A dermoscopy image of a single skin lesion:
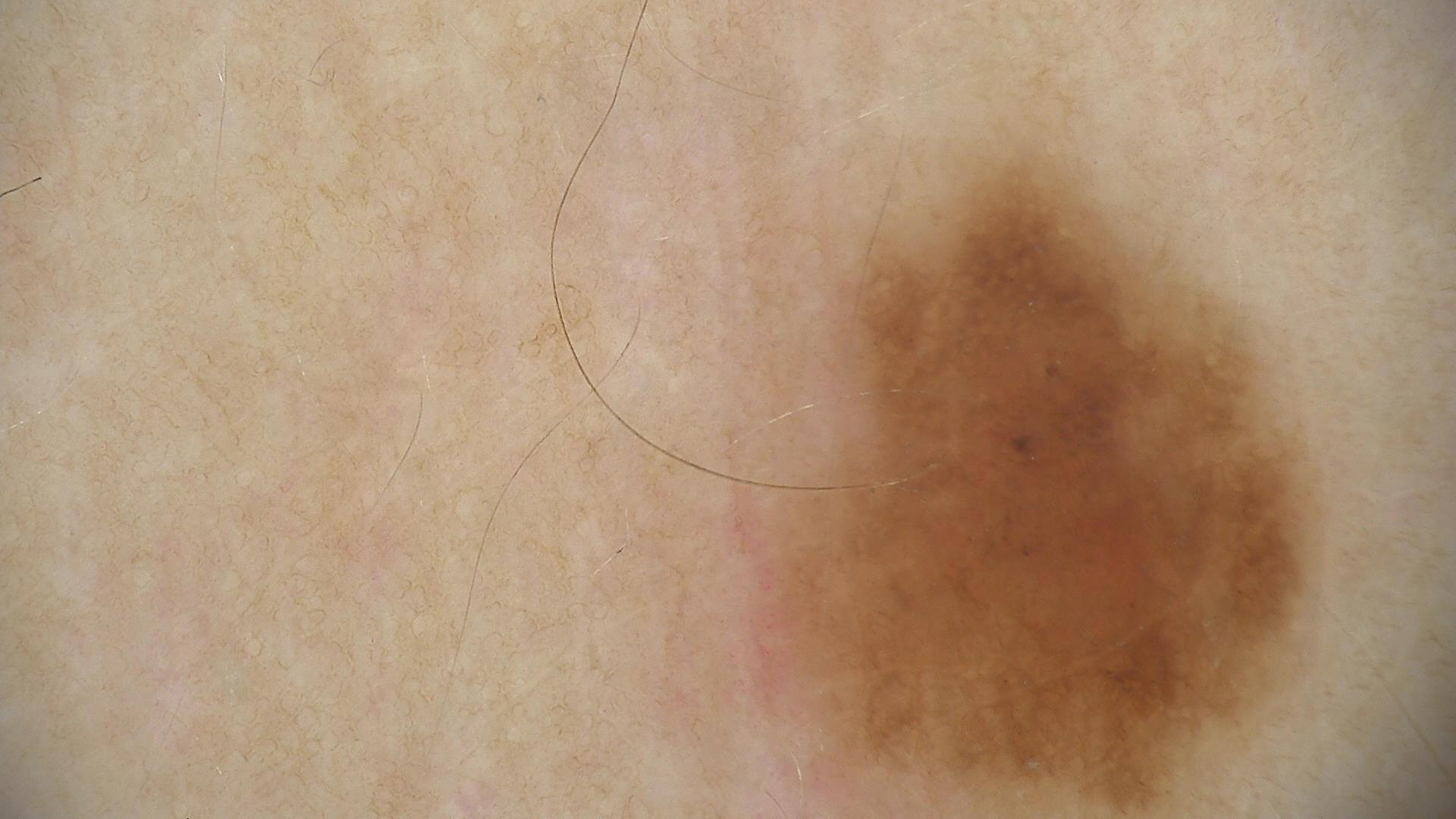| key | value |
|---|---|
| diagnosis | dysplastic junctional nevus (expert consensus) |